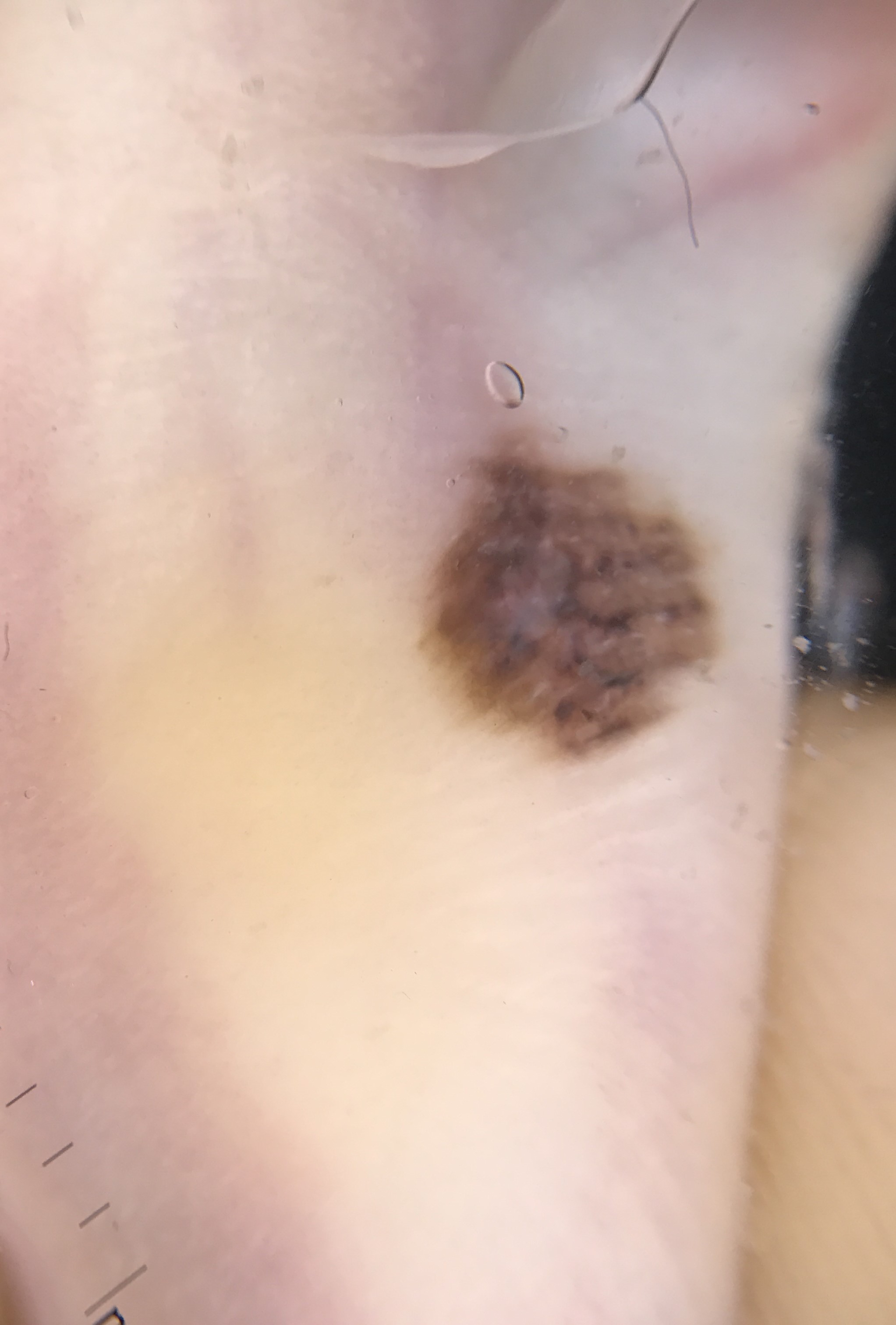Q: What is this lesion?
A: acral dysplastic compound nevus (expert consensus)